A female subject 66 years old · a clinical photograph showing a skin lesion — 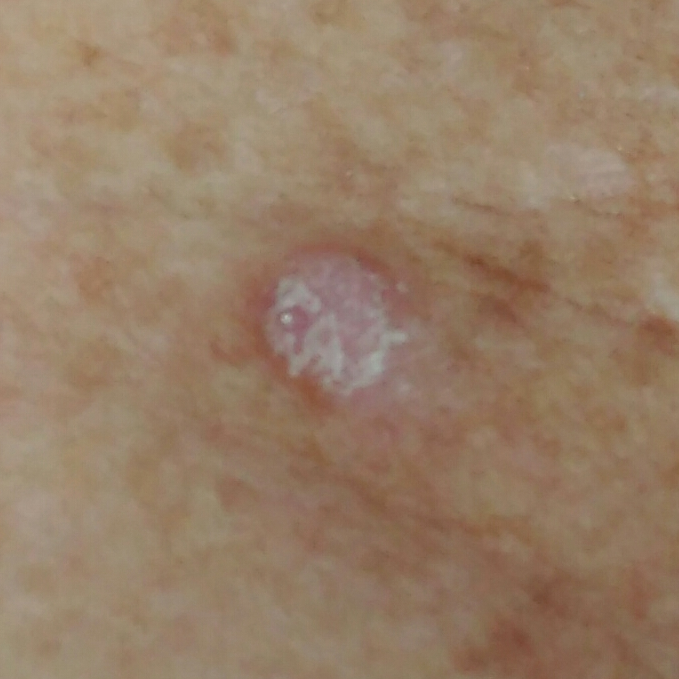| feature | finding |
|---|---|
| location | the chest |
| patient-reported symptoms | elevation, itching |
| pathology | actinic keratosis (biopsy-proven) |